This is a close-up image — 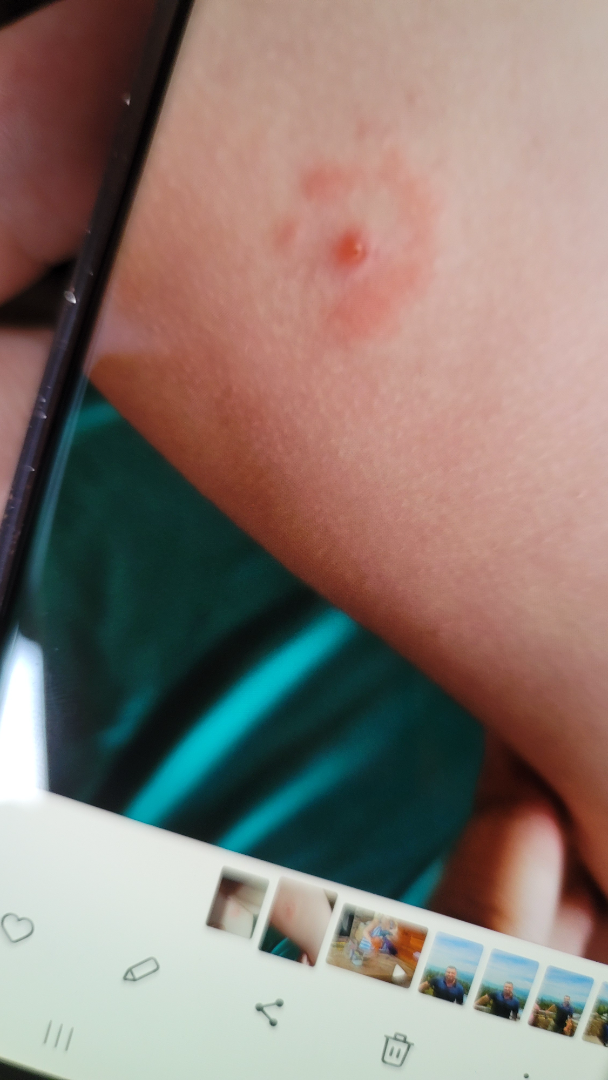assessment = not assessable.